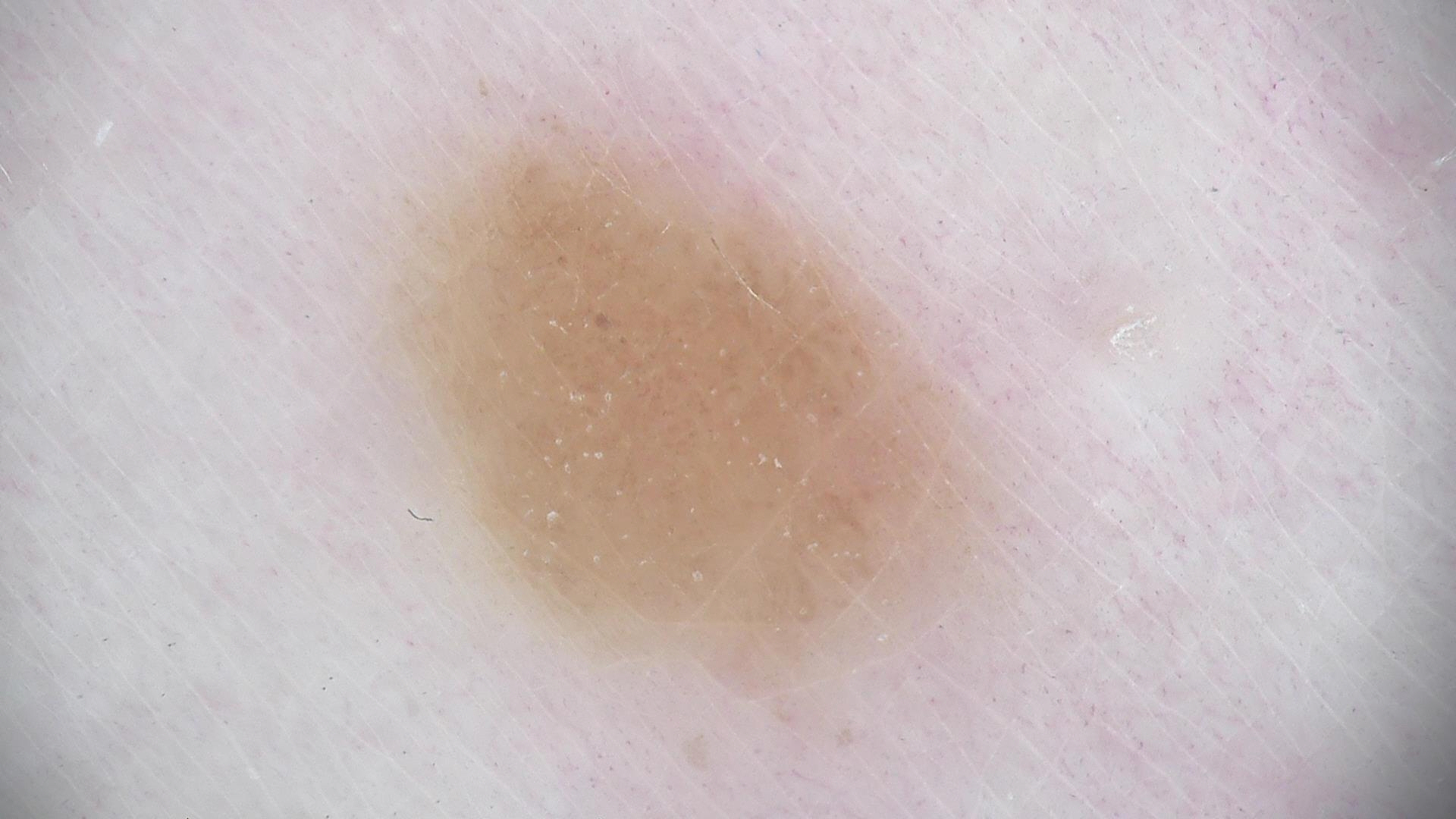image = dermoscopy; lesion type = banal; class = dermal nevus (expert consensus).